A dermatoscopic image of a skin lesion:
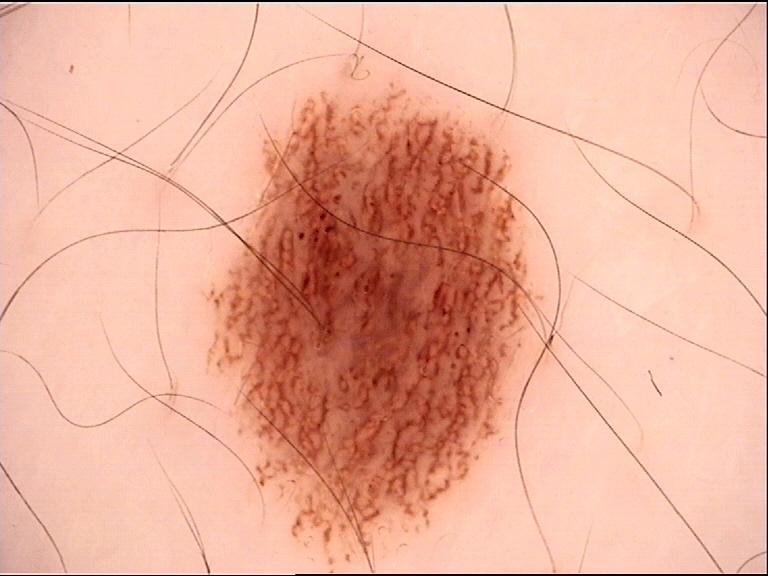Q: What was the diagnostic impression?
A: dysplastic junctional nevus (expert consensus)